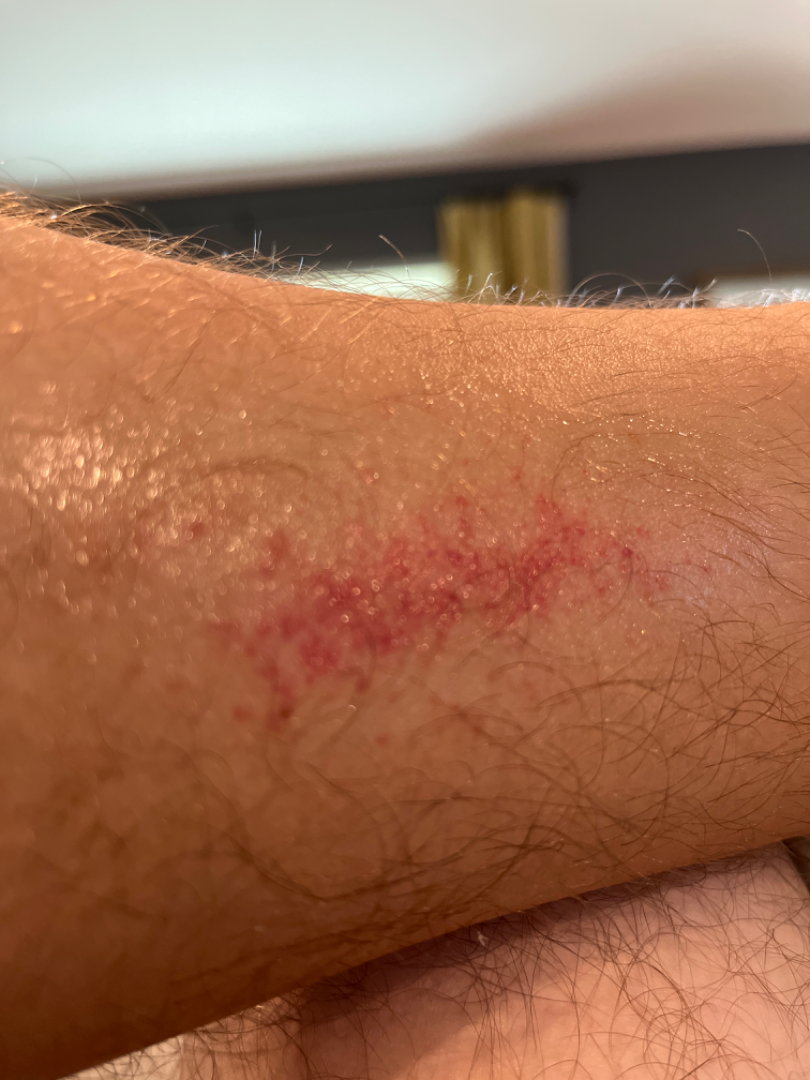assessment: could not be assessed | affected area: leg | lesion texture: flat and raised or bumpy | present for: less than one week | photo taken: close-up | patient describes the issue as: a rash | patient: male, age 30–39 | symptoms: itching.